The lesion is described as raised or bumpy and rough or flaky. The affected area is the arm, leg, back of the hand and top or side of the foot. Reported duration is about one day. Associated systemic symptoms include mouth sores, shortness of breath and fatigue. Symptoms reported: burning, bothersome appearance, darkening, enlargement, pain and itching. The photo was captured at a distance — 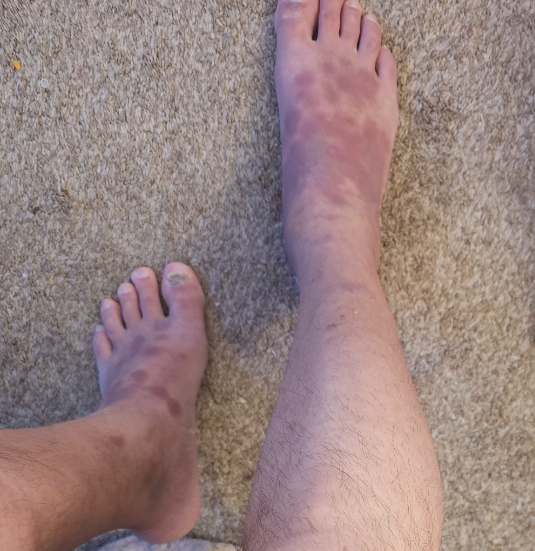Assessment: On remote dermatologist review: Lichen Simplex Chronicus, Eczema and Psoriasis were each considered, in no particular order; less probable is Drug Rash; a remote consideration is Erythema multiforme; lower on the differential is Acute and chronic dermatitis; less likely is Stasis Dermatitis; a more distant consideration is Lichen planus/lichenoid eruption.